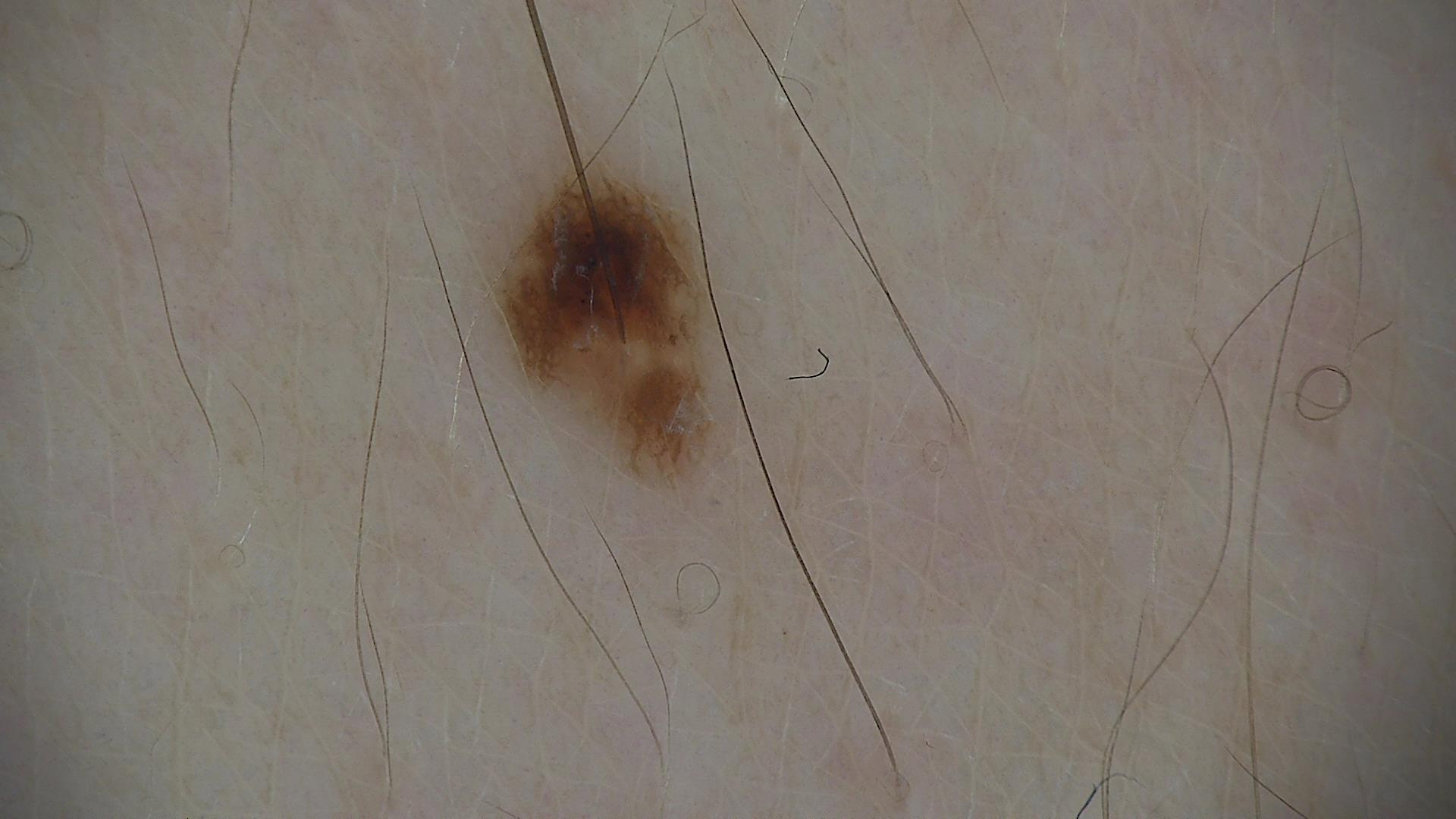* assessment — dysplastic junctional nevus (expert consensus)